An image taken at an angle — 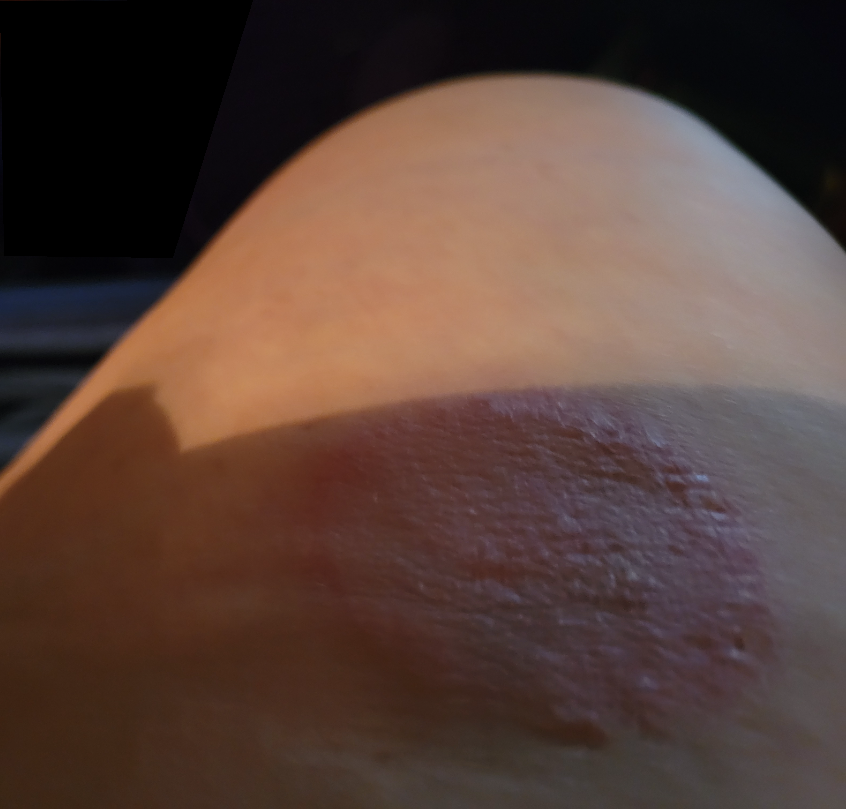On photographic review: Tinea (weight 0.67); Eczema (weight 0.33).